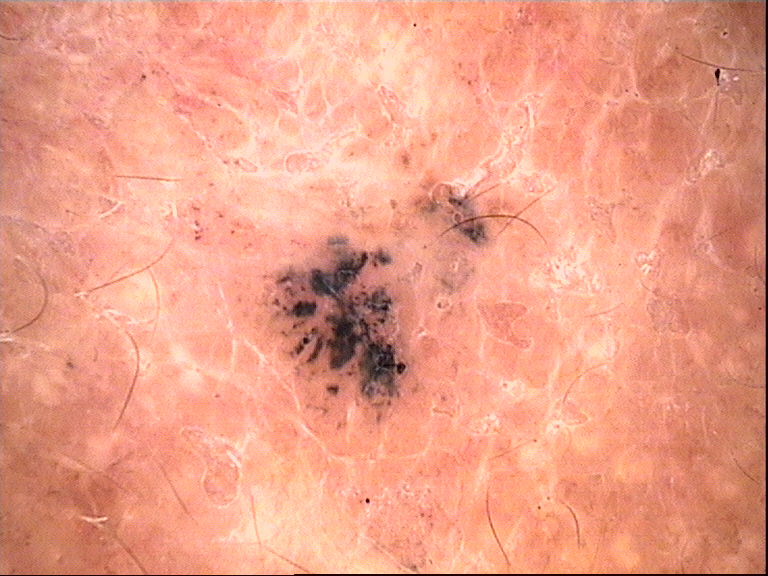diagnostic label = basal cell carcinoma (biopsy-proven).